The affected area is the leg · the photo was captured at an angle:
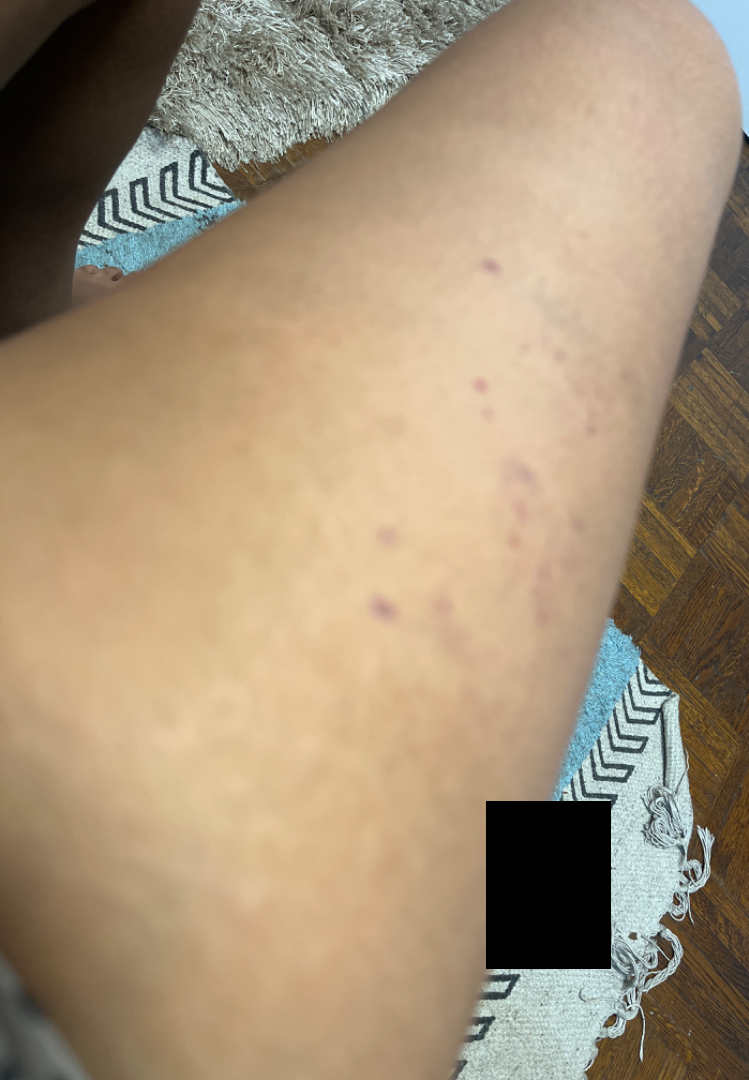assessment=could not be assessed | history=less than one week | surface texture=flat | skin tone=lay graders estimated a MST of 3.